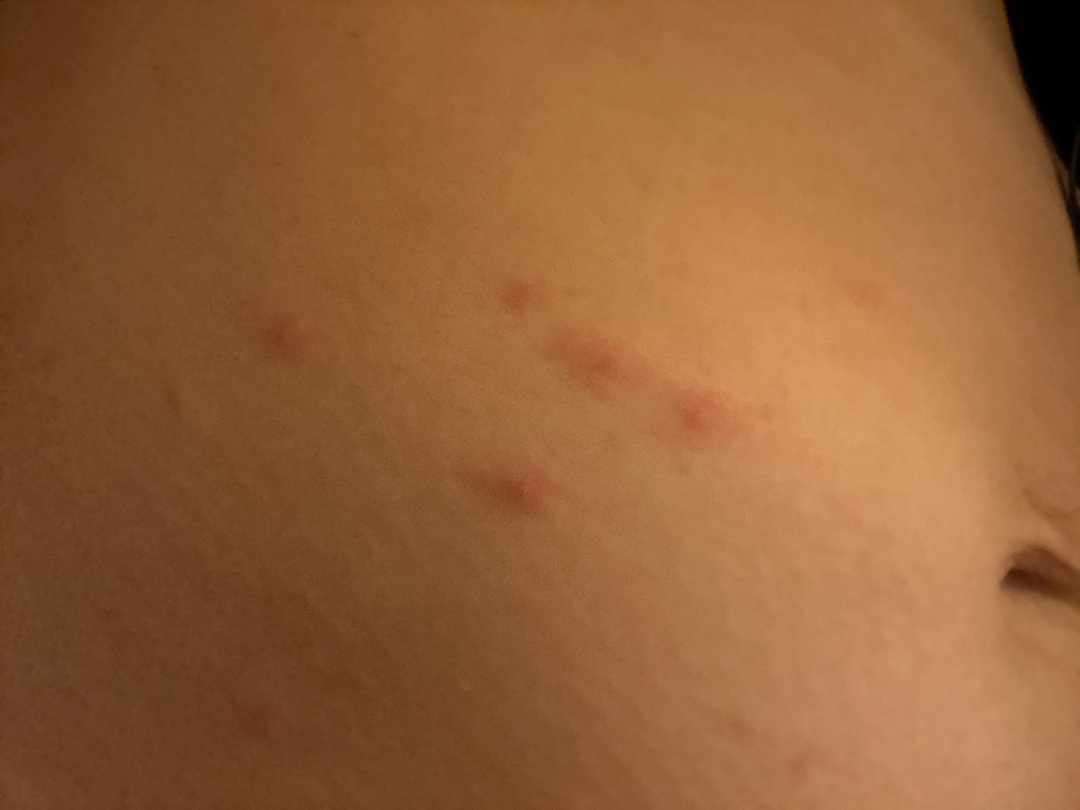Q: Who is the patient?
A: female, age 18–29
Q: Fitzpatrick or Monk tone?
A: FST III; lay reviewers estimated Monk skin tone scale 4 (US pool) or 3 (India pool)
Q: What is the framing?
A: close-up
Q: What is the dermatologist's impression?
A: Scabies (0.50); Insect Bite (0.50)